An image taken at an angle; the patient reported no systemic symptoms; the affected area is the leg, arm and back of the hand; the patient described the issue as a growth or mole; the patient notes the lesion is raised or bumpy, rough or flaky and fluid-filled.
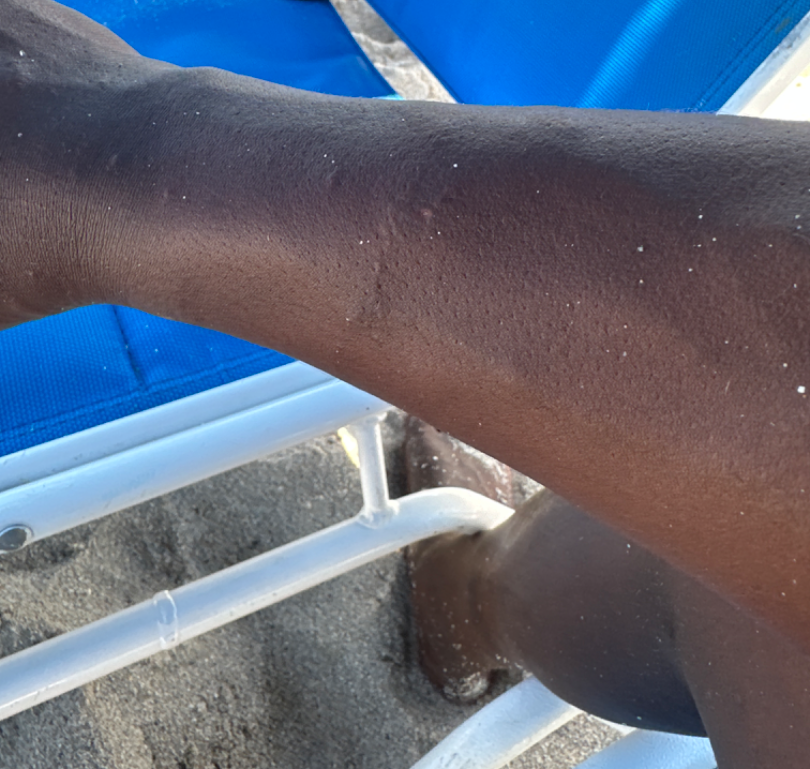| key | value |
|---|---|
| assessment | could not be assessed |